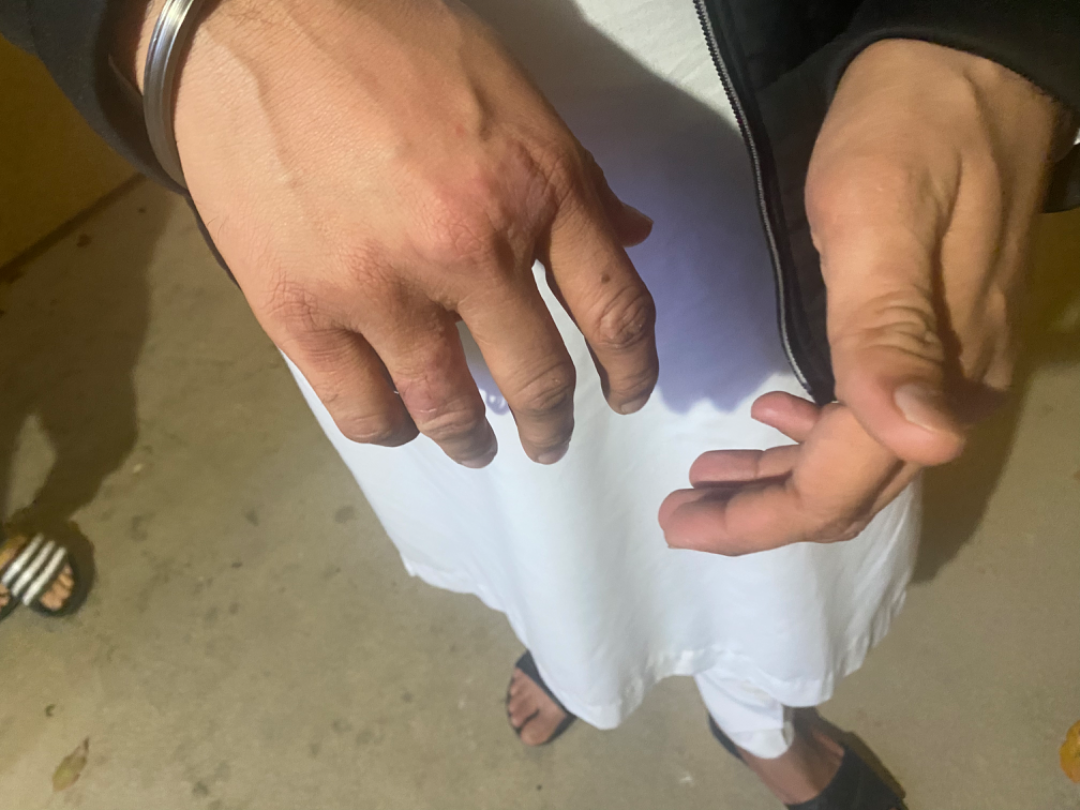Notes:
• assessment: indeterminate from the photograph
• image framing: at a distance